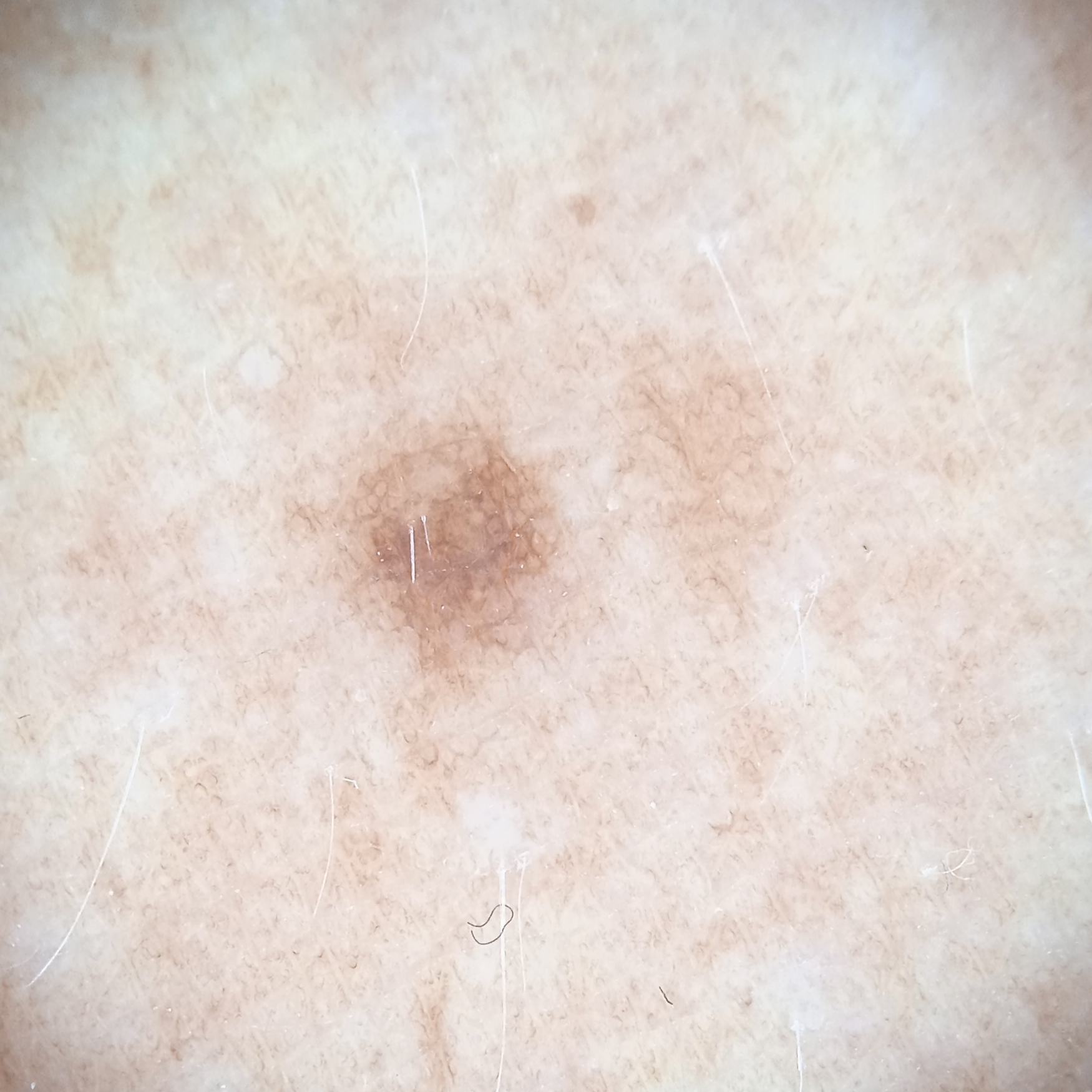The lesion was assessed as a melanocytic nevus.